Dermoscopy of a skin lesion.
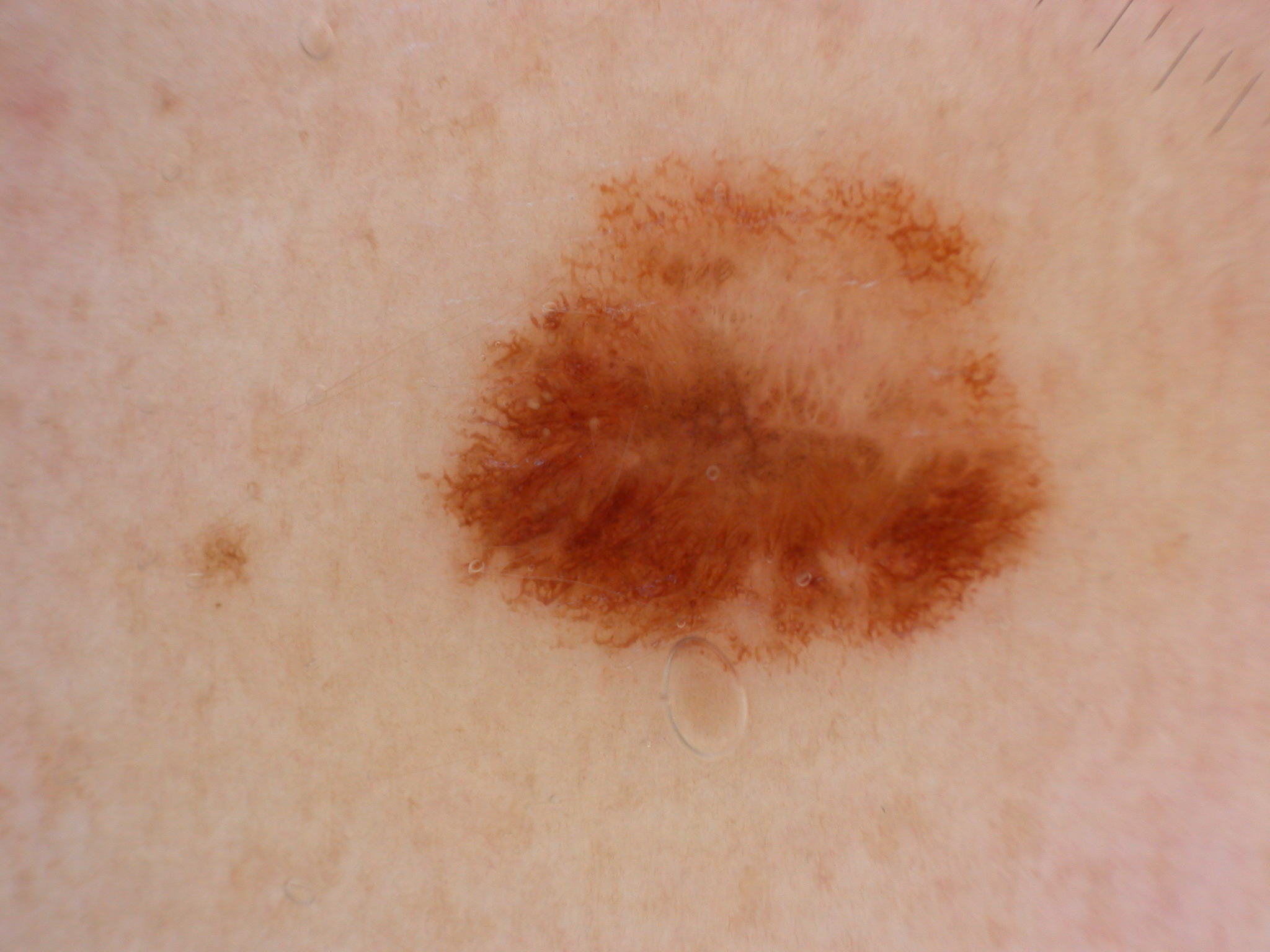location = [409, 143, 1068, 687]
assessment = a benign lesion